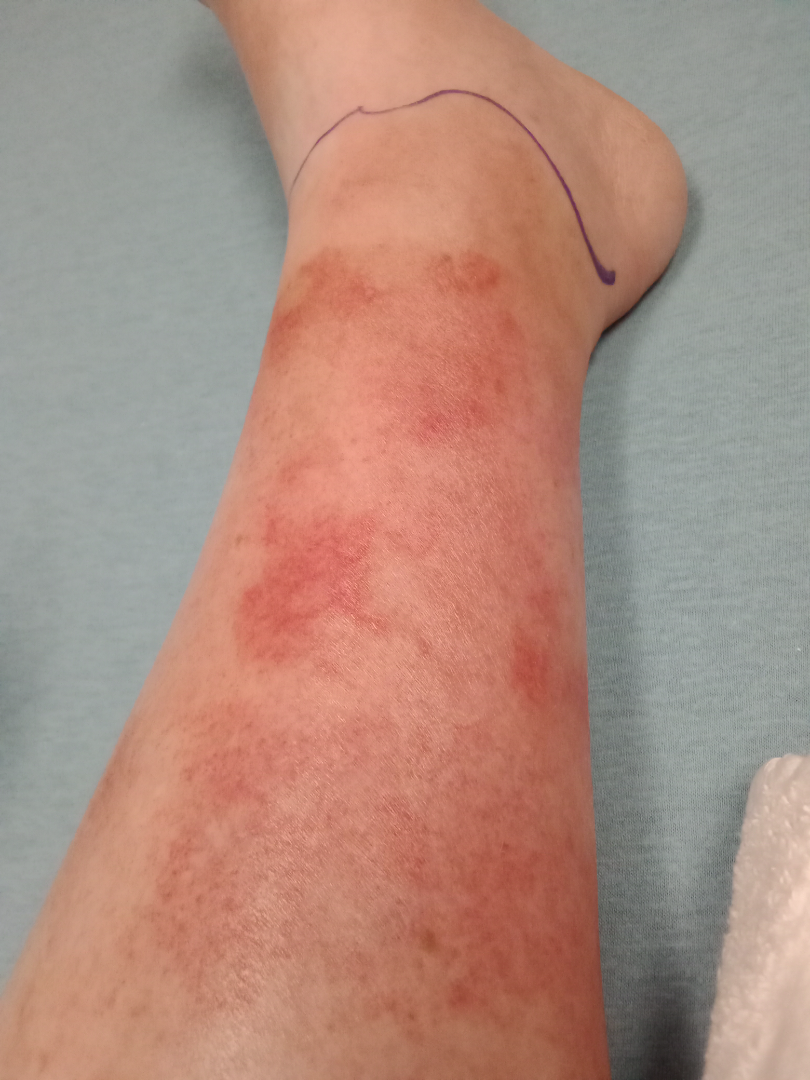Q: What is the differential diagnosis?
A: the leading impression is Cellulitis; an alternative is Stasis Dermatitis; possibly Pigmented purpuric eruption